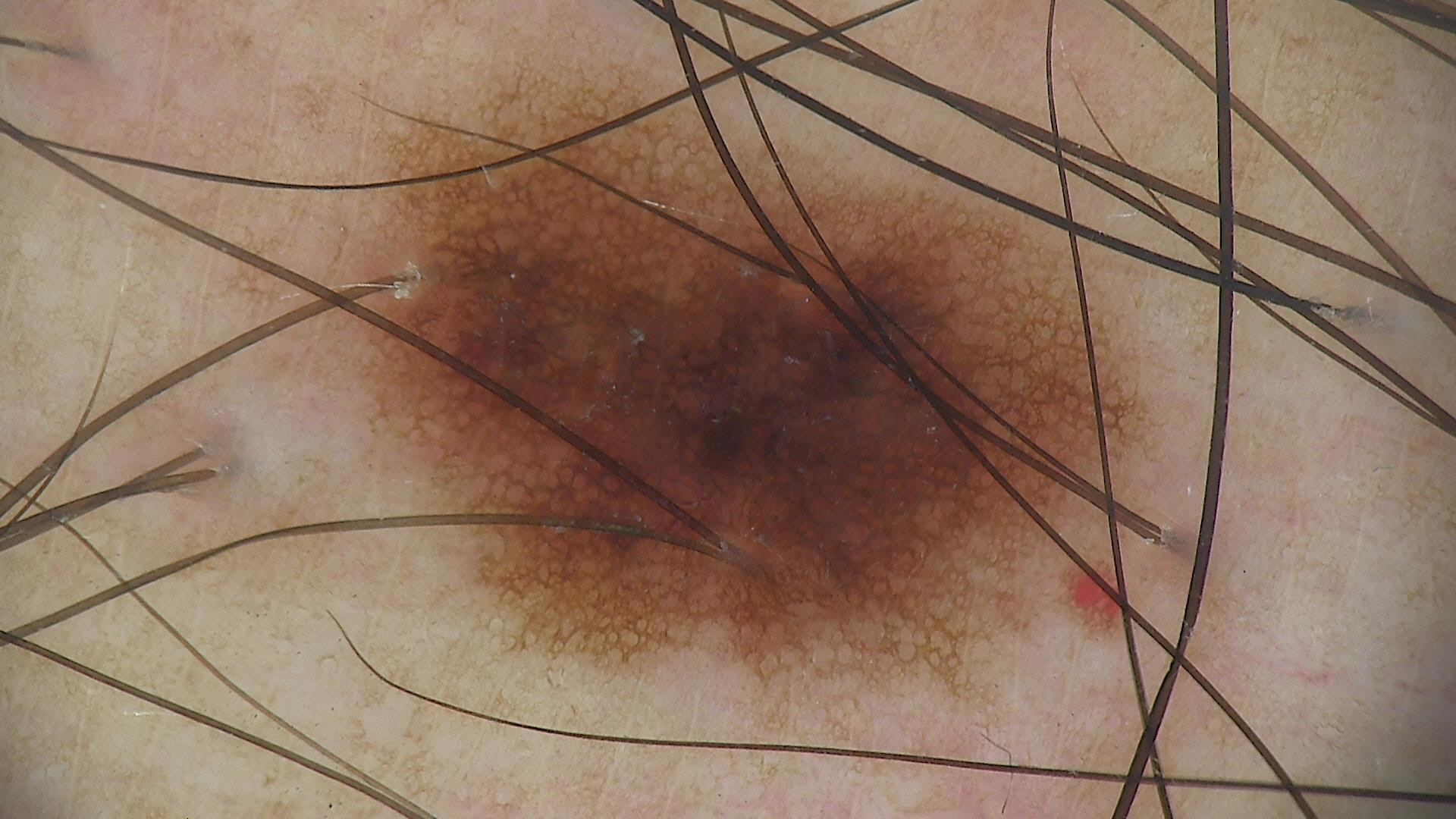diagnosis = dysplastic junctional nevus (expert consensus).